The head or neck, back of the hand, back of the torso, arm, leg and top or side of the foot are involved. An image taken at an angle. The patient is 40–49, female. The patient reports the condition has been present for less than one week: 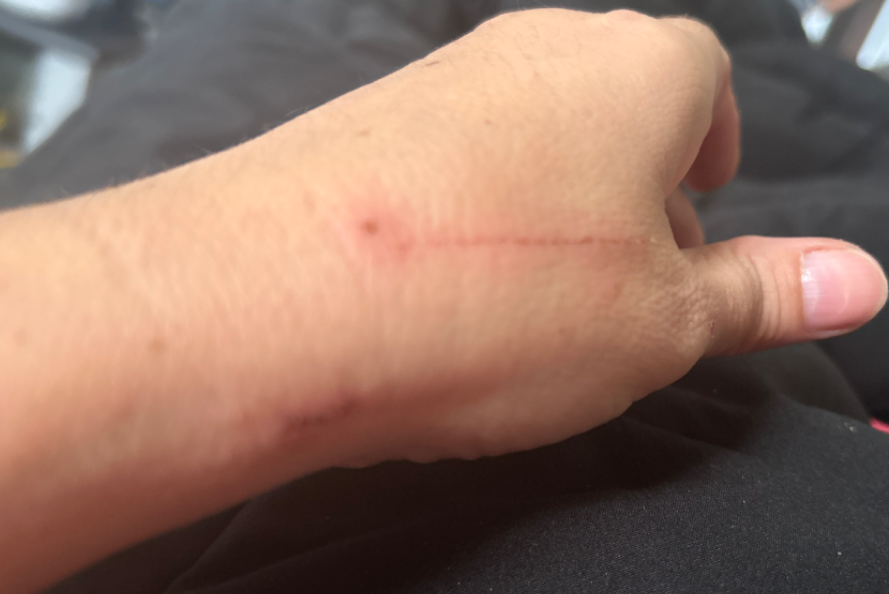Case summary:
- assessment: could not be assessed